A skin lesion imaged with a dermatoscope:
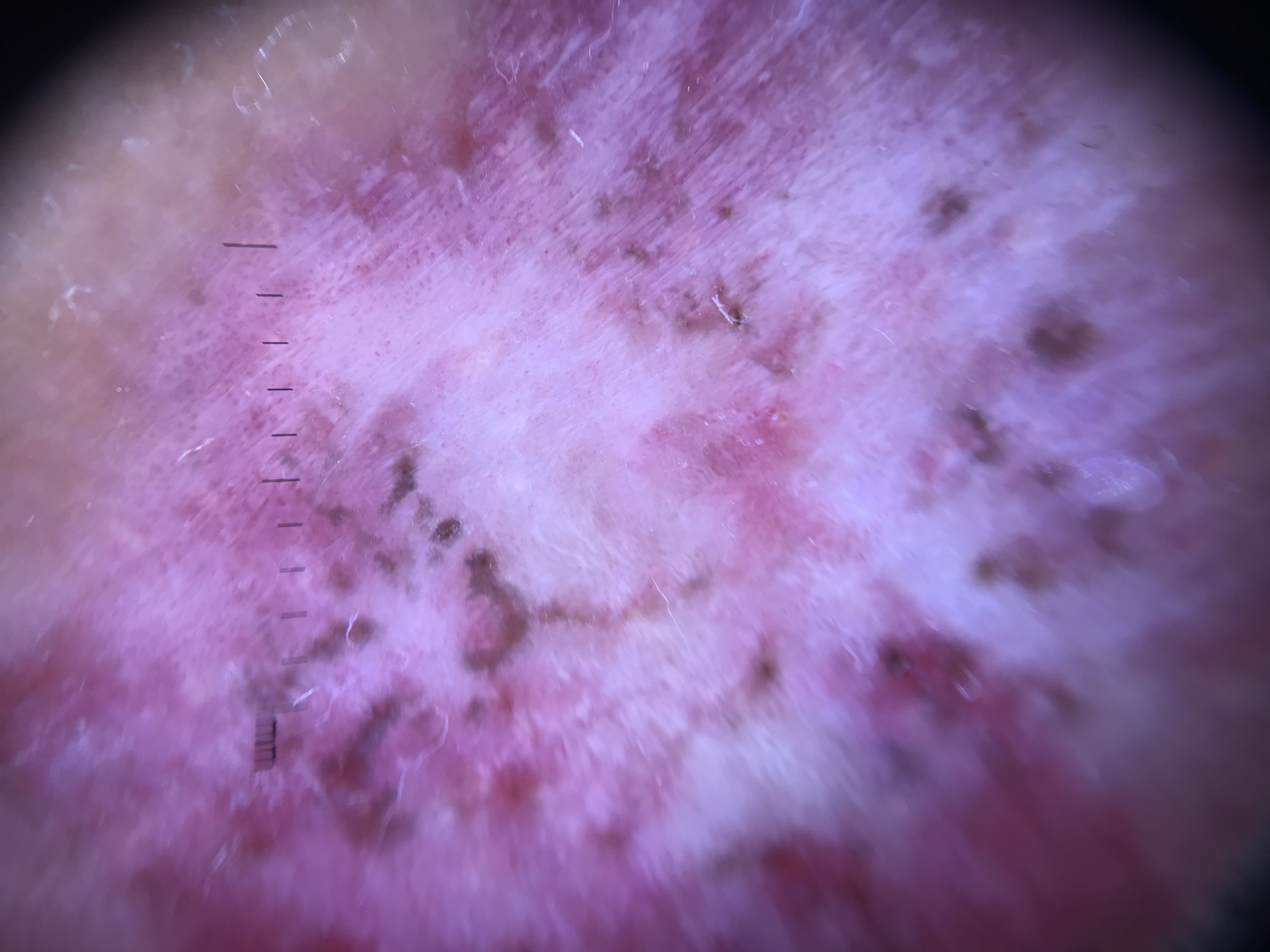label — basal cell carcinoma (biopsy-proven)